A contact-polarized dermoscopy image of a skin lesion. A female subject about 70 years old — 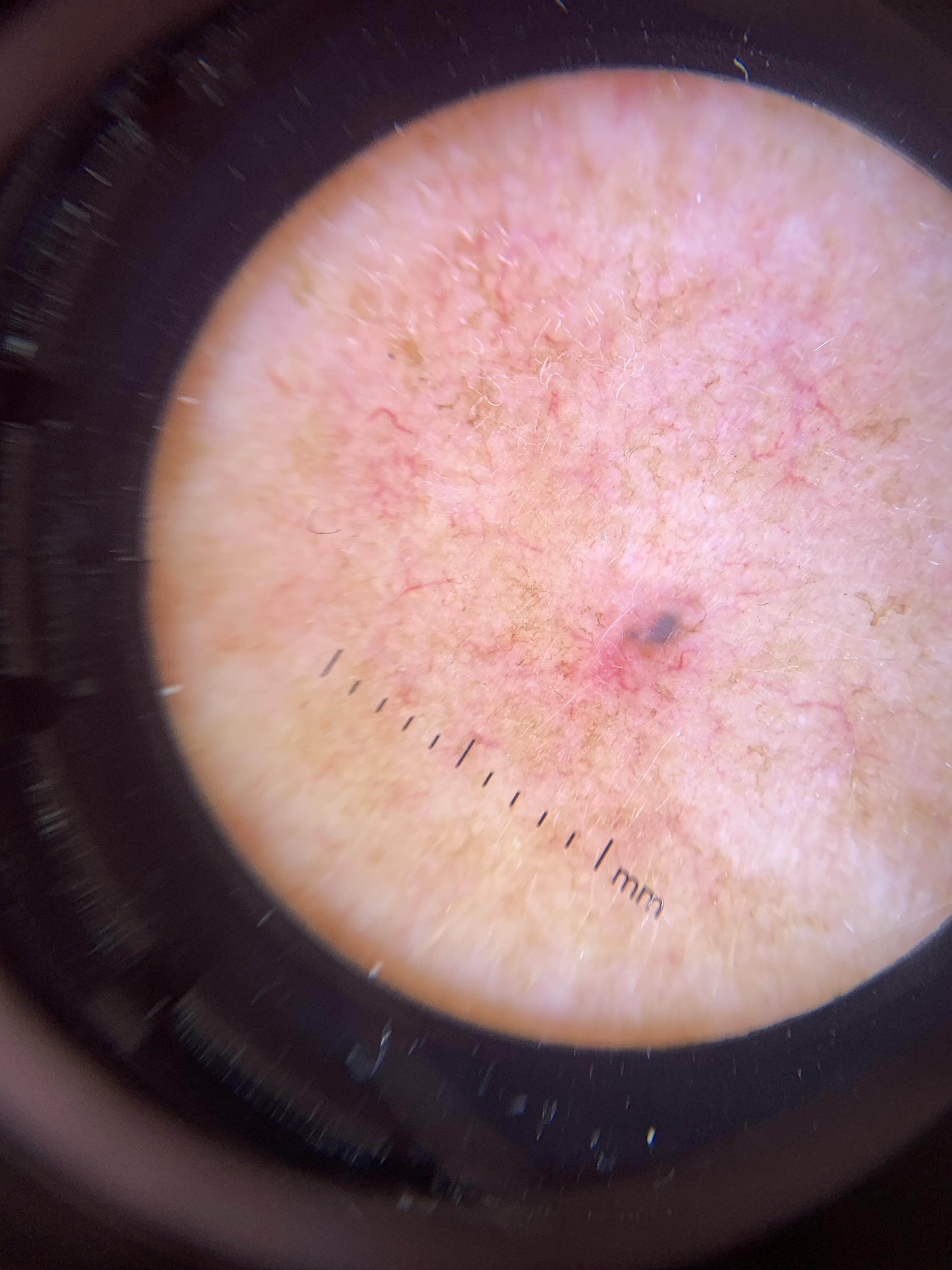Located on the head or neck.
Biopsy-confirmed as a basal cell carcinoma.